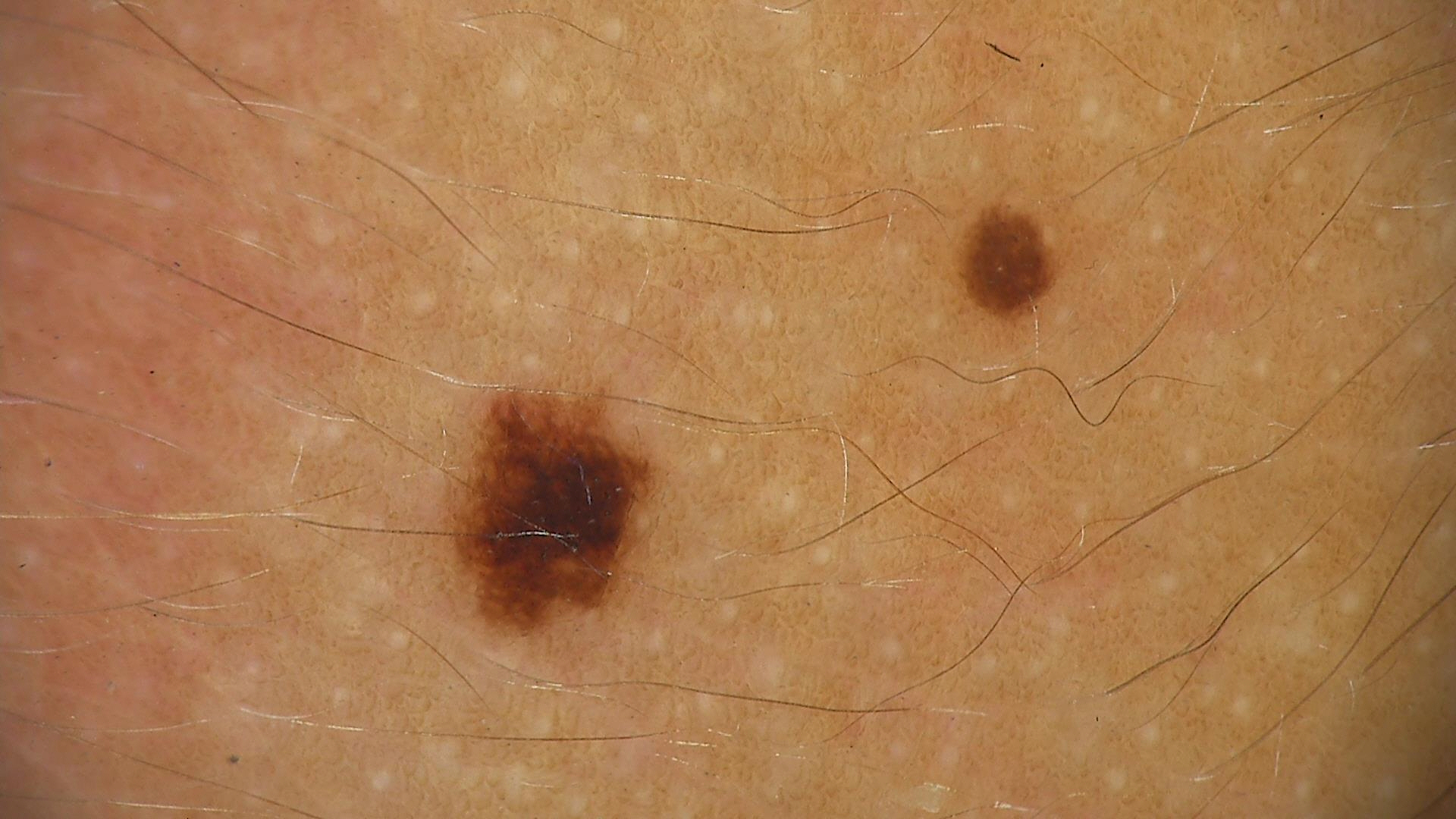Summary: A skin lesion imaged with a dermatoscope. Impression: Diagnosed as a benign lesion — a dysplastic junctional nevus.